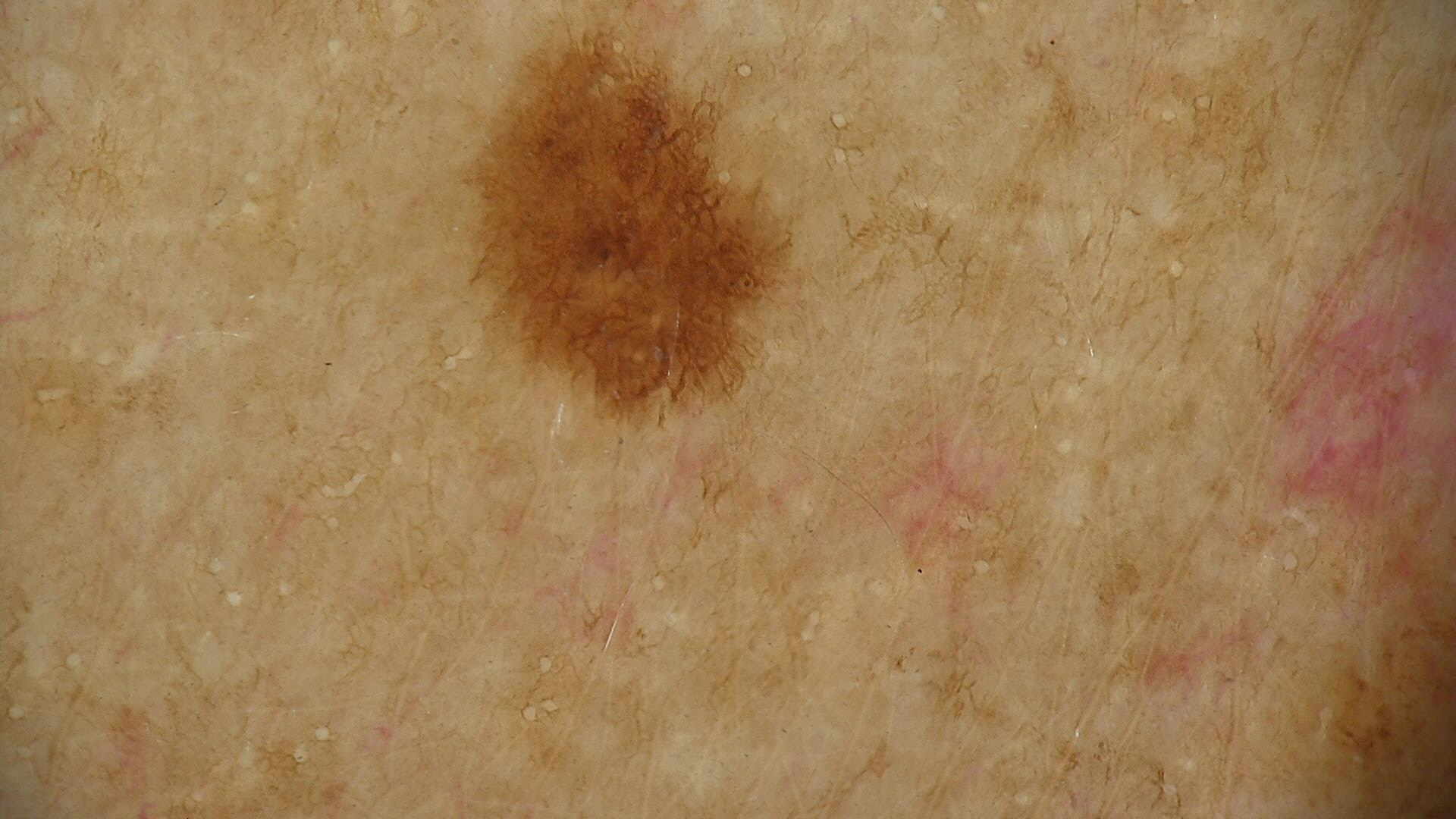Findings:
– label: dysplastic junctional nevus (expert consensus)